A clinical photograph showing a skin lesion; by self-report, a personal history of cancer, a family history of skin cancer, no prior organ transplant, and no sunbed use; a female subject 64 years of age; a moderate number of moles by the patient's own estimate; the patient says their skin tans without first burning: 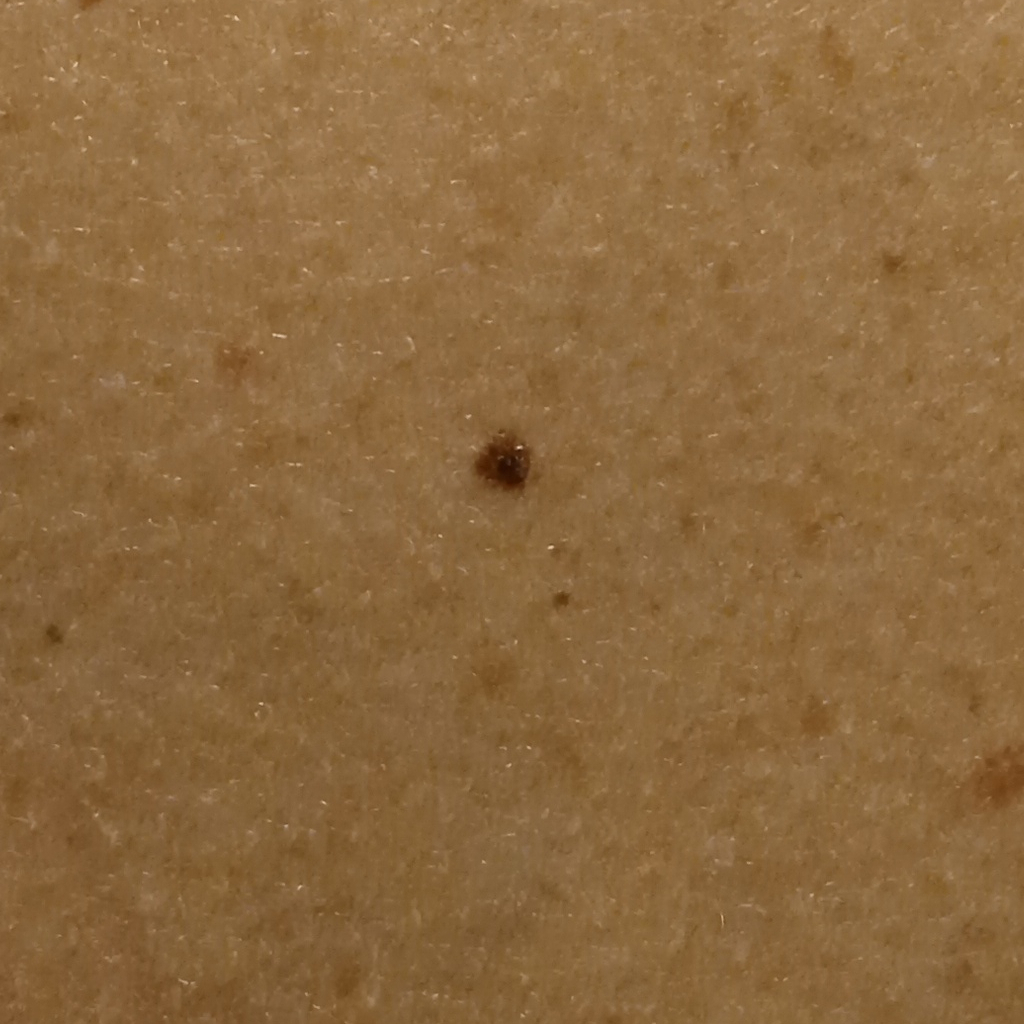Findings: The lesion involves the back. Diagnosis: Confirmed on histopathology as a seborrheic keratosis, following excision.